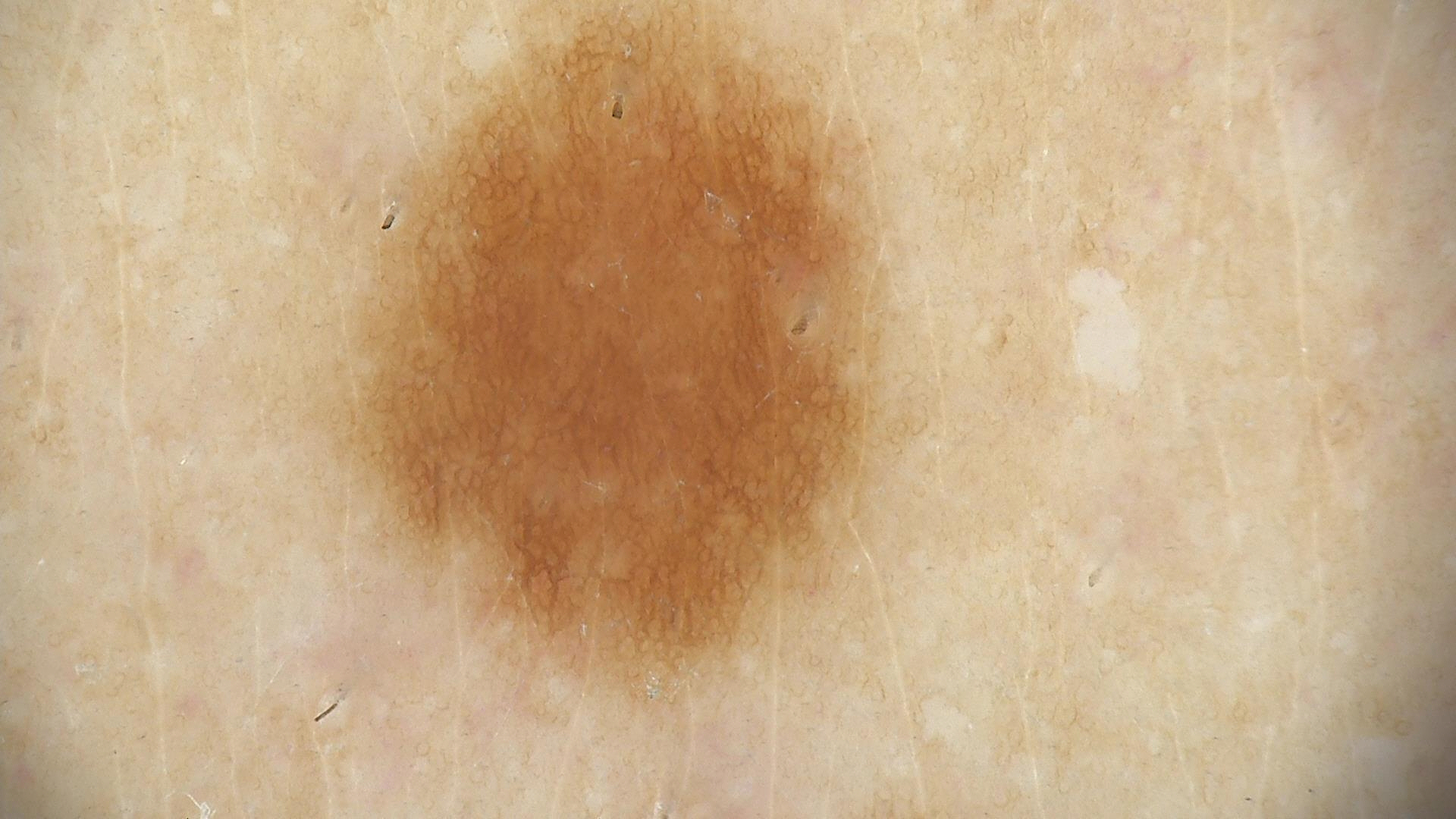Case:
A dermoscopy image of a single skin lesion.
Impression:
The diagnostic label was a benign lesion — a dysplastic junctional nevus.